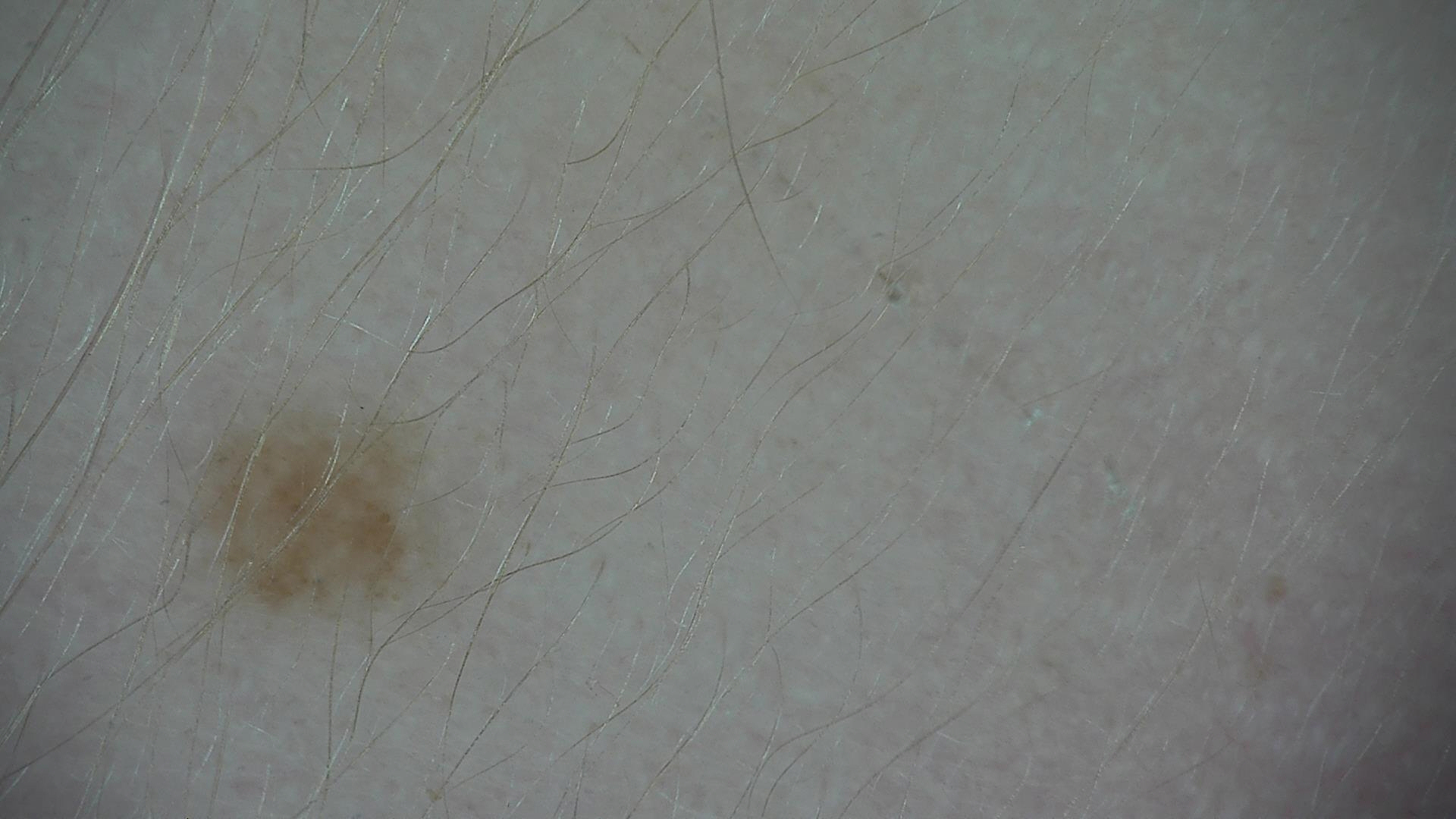  diagnosis:
    name: junctional nevus
    code: jb
    malignancy: benign
    super_class: melanocytic
    confirmation: expert consensus